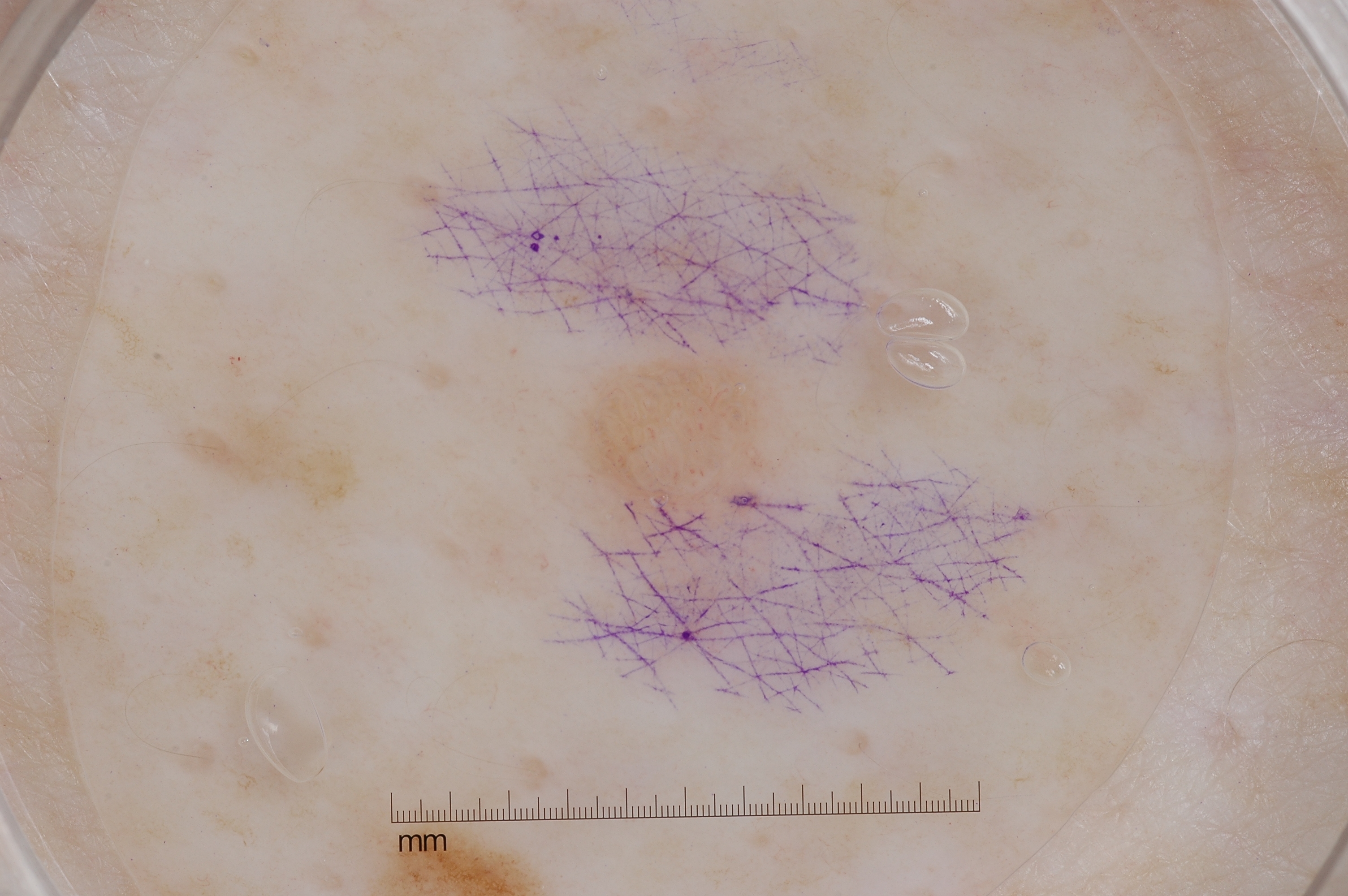This is a dermoscopic photograph of a skin lesion. The lesion's extent is 569/350/779/553. The clinical diagnosis was a seborrheic keratosis, a benign lesion.